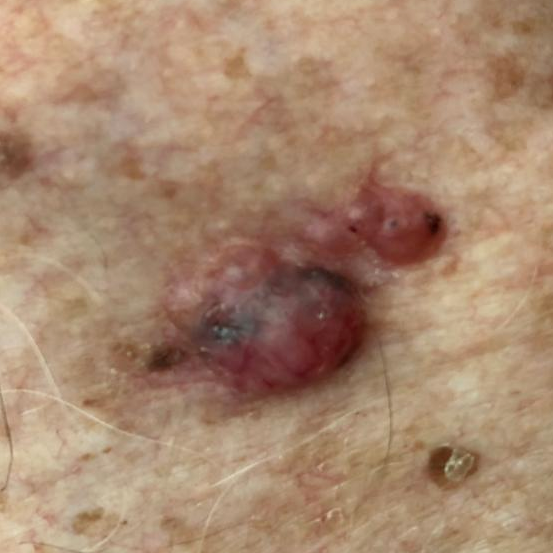A male subject aged 79. A clinical close-up photograph of a skin lesion. The lesion is located on the chest. The patient reports that the lesion itches, has grown, and is elevated, but does not hurt and has not bled. On biopsy, the diagnosis was a basal cell carcinoma.